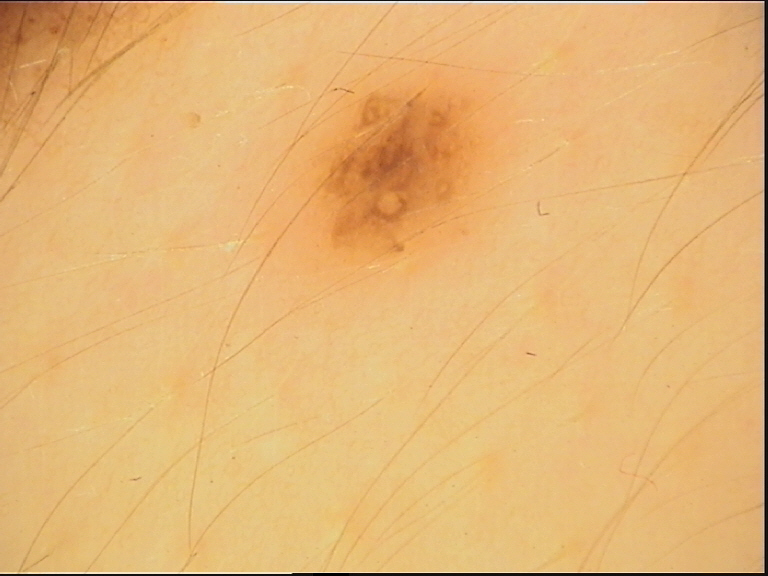Labeled as a dysplastic junctional nevus.